The patient was assessed as Fitzpatrick II; a clinical photograph of a skin lesion; the chart notes a previous melanoma but no melanoma in first-degree relatives; a male patient aged approximately 75 — 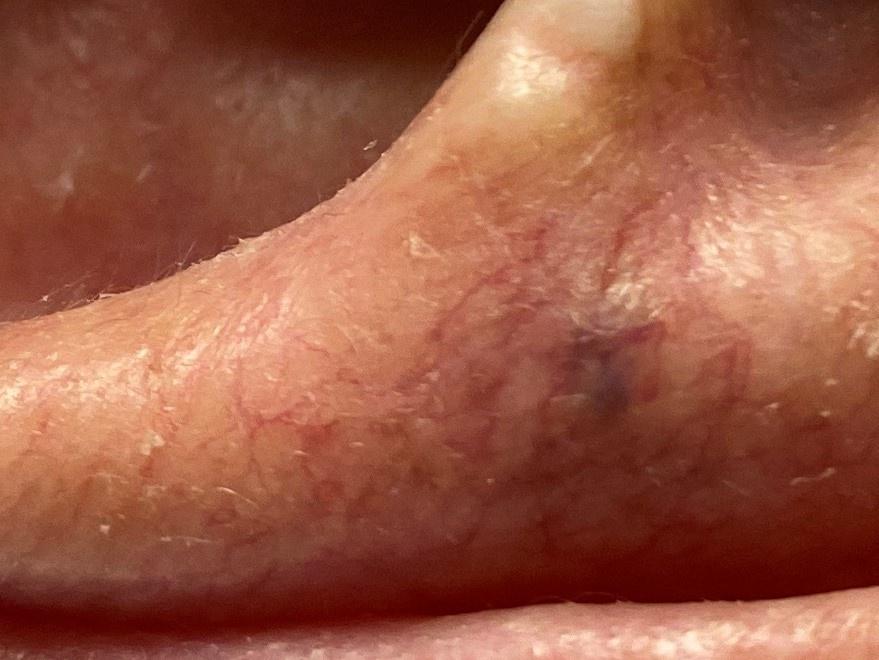lesion_location:
  region: the head or neck
diagnosis:
  name: vascular lesion
  malignancy: benign
  confirmation: expert clinical impression